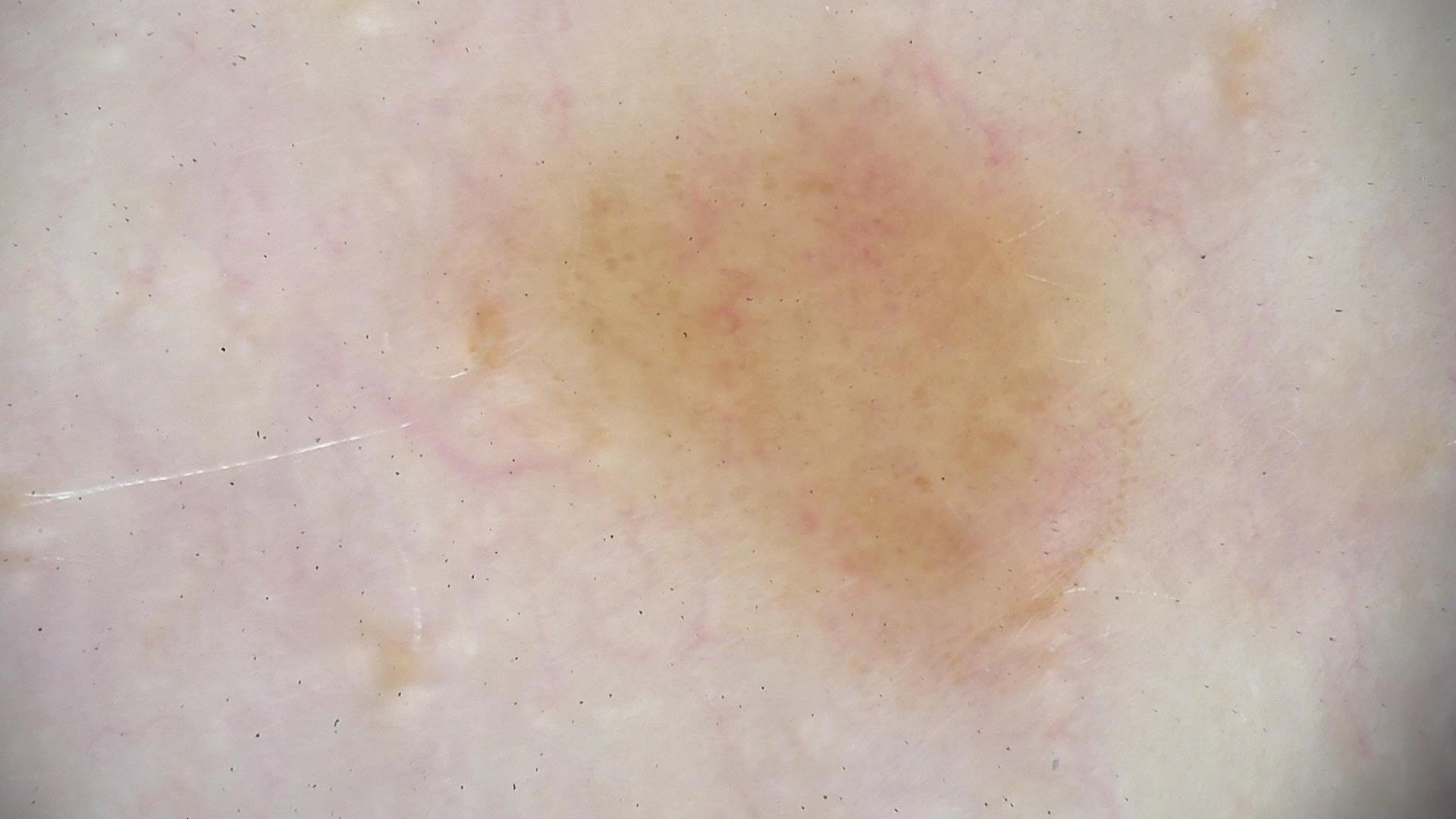A dermoscopic image of a skin lesion. Consistent with a benign lesion — a dysplastic junctional nevus.